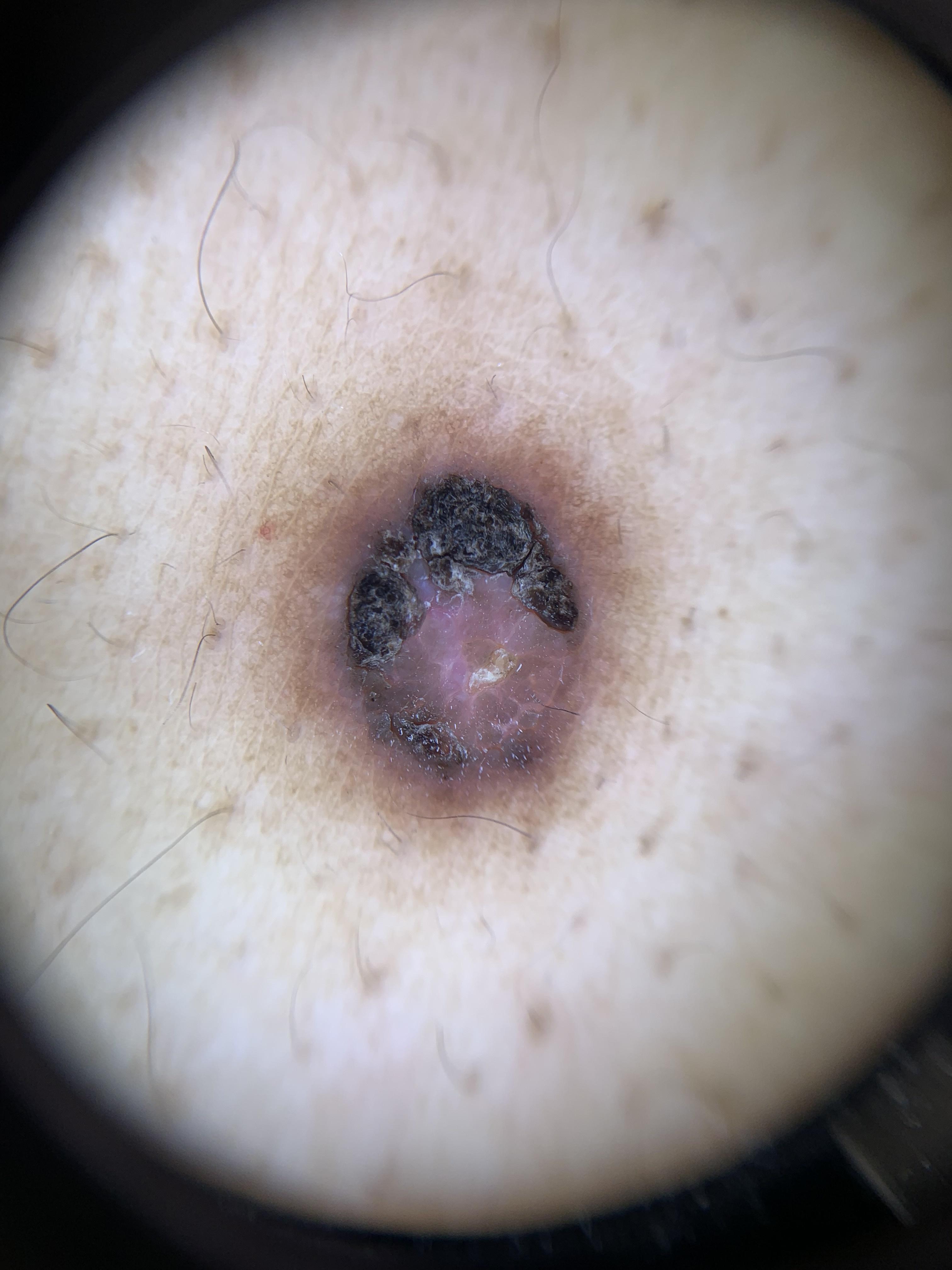A female patient aged 38 to 42. A contact-polarized dermoscopy image of a skin lesion. Fitzpatrick III. Located on a lower extremity. Histopathological examination showed a fibro-histiocytic lesion — a dermatofibroma.